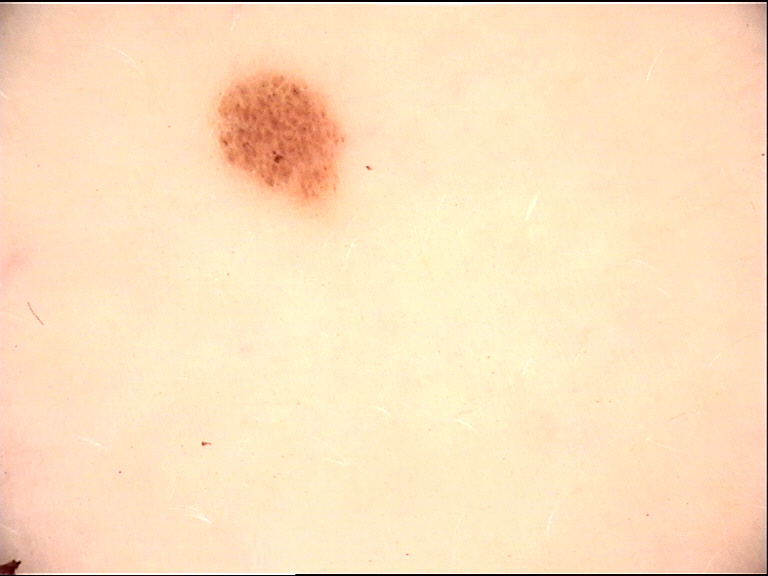Classified as a benign lesion — a dysplastic junctional nevus.